The leg is involved, the subject is a female aged 50–59, the photo was captured at an angle.
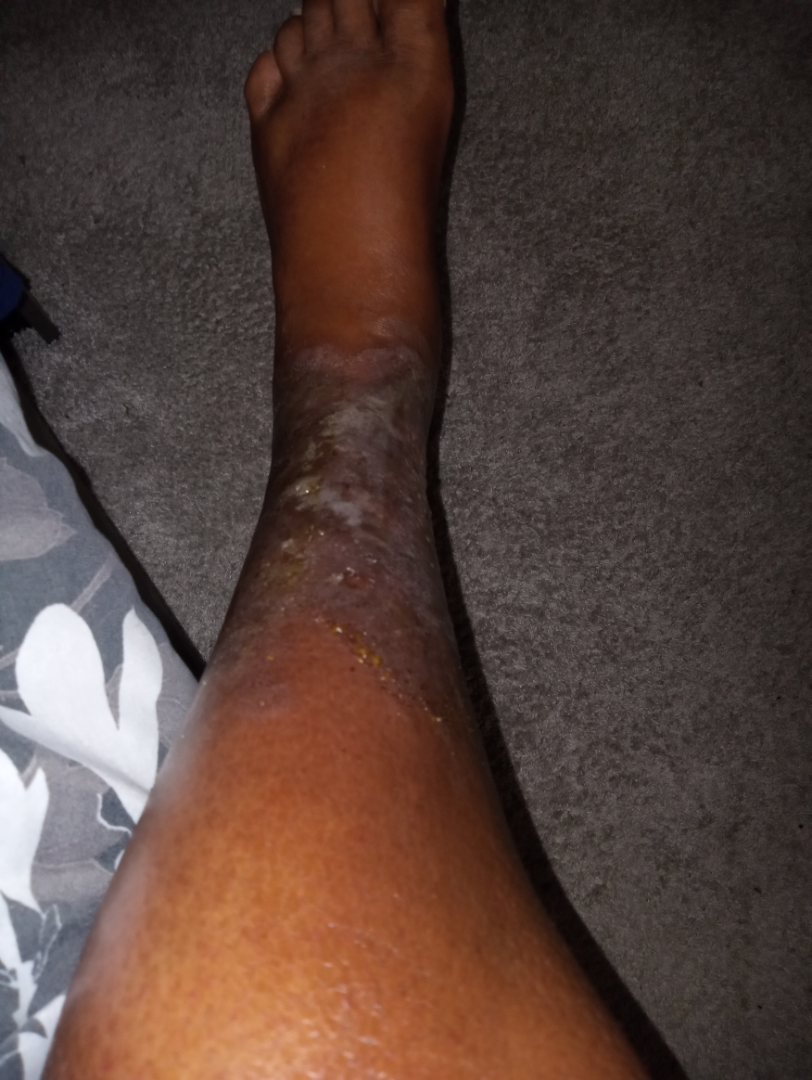dermatologist impression = single-reviewer assessment: most consistent with Infected eczema; also on the differential is Stasis Dermatitis.